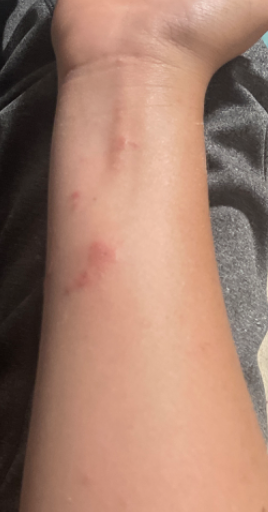symptoms = itching
subject = female
patient describes the issue as = a rash
symptom duration = less than one week
image framing = at a distance
body site = head or neck, palm and arm
texture = raised or bumpy
differential = Allergic Contact Dermatitis (most likely); Scabies (lower probability); Acute dermatitis, NOS (lower probability); Insect Bite (lower probability)